The patient reports no personal history of skin cancer; a macroscopic clinical photograph of a skin lesion:
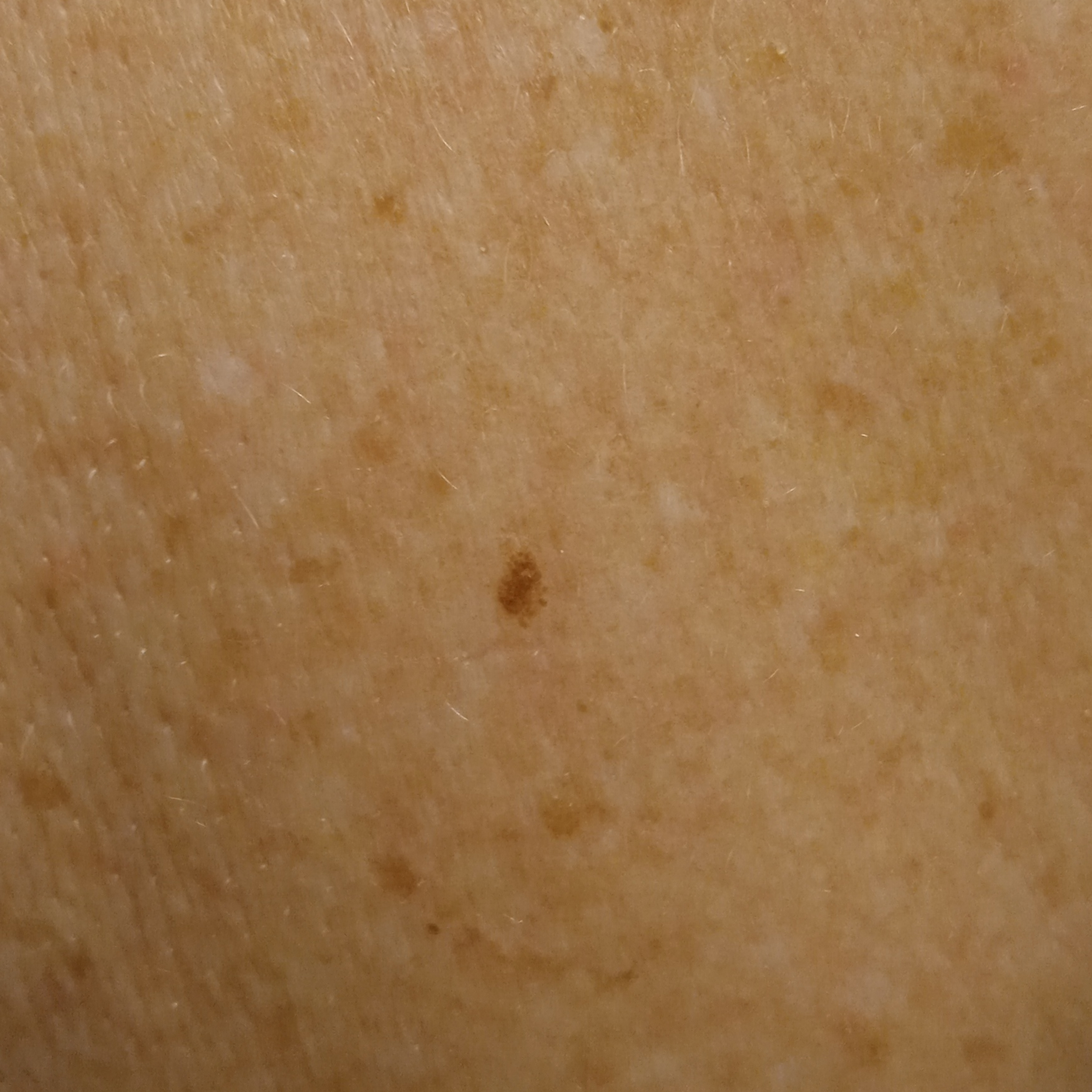  lesion_size:
    diameter_mm: 3.9
  diagnosis:
    name: seborrheic keratosis
    malignancy: benign